Dermoscopy of a skin lesion.
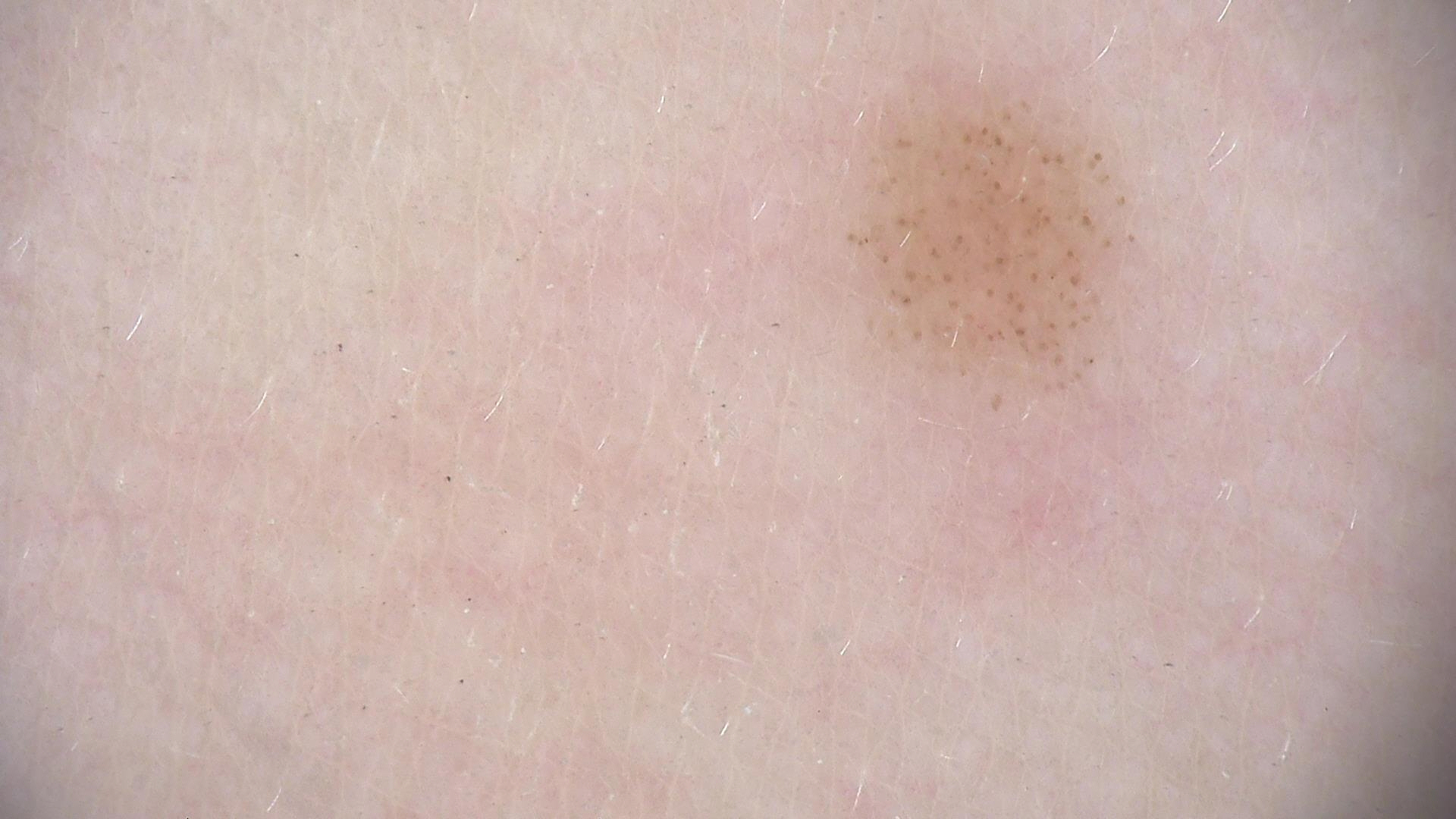diagnostic label = dysplastic junctional nevus (expert consensus).